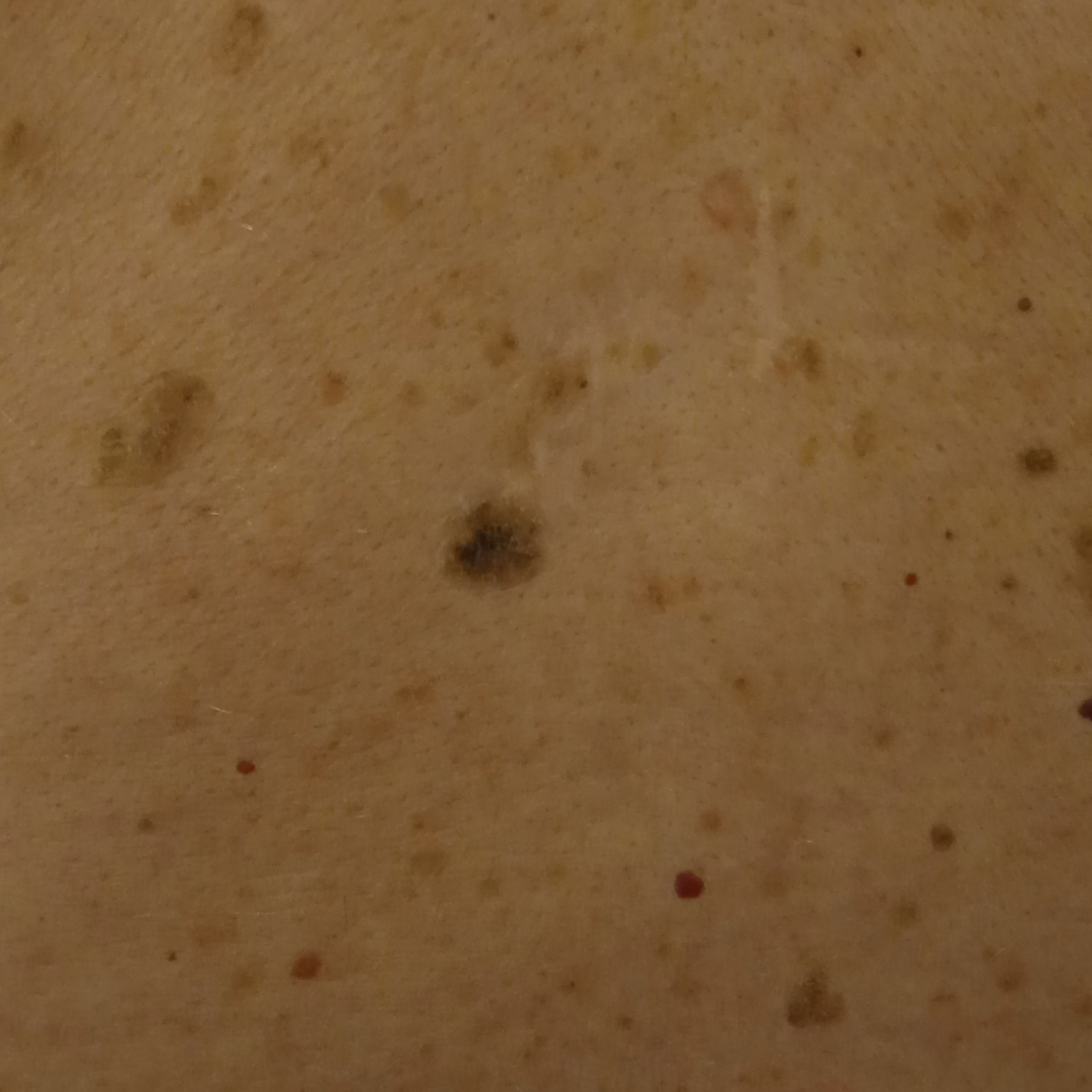Case:
• subject · male, 78 years of age
• clinical context · research study (no referral diagnosis)
• sun reaction · skin reddens with sun exposure
• risk factors · a personal history of cancer
• nevus count · few melanocytic nevi overall
• imaging · clinical photograph
• location · the back
• diameter · 11 mm
• assessment · seborrheic keratosis (dermatologist consensus)